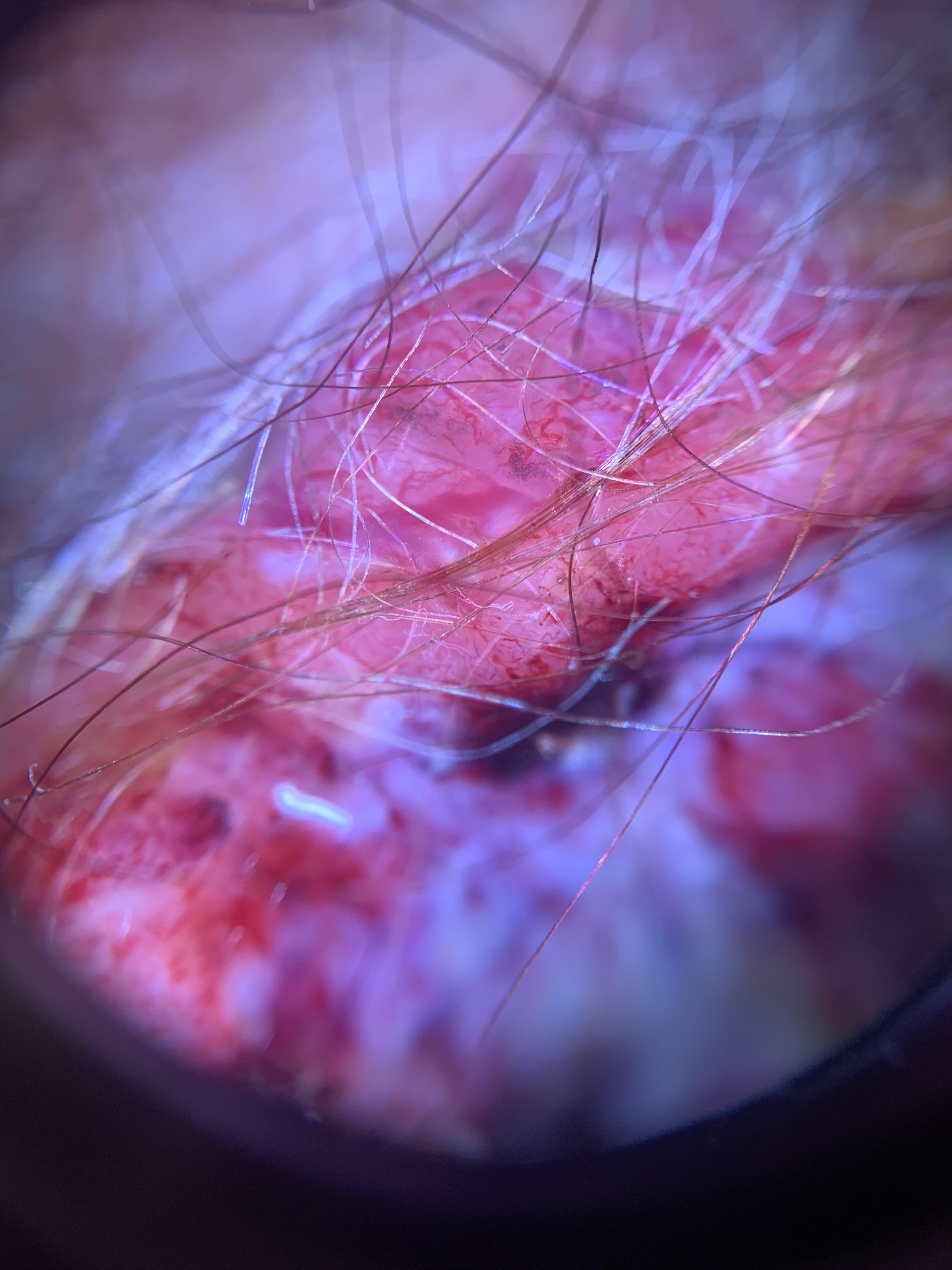| key | value |
|---|---|
| imaging | dermoscopic image |
| subject | female, roughly 85 years of age or older |
| site | the head or neck |
| diagnostic label | Squamous cell carcinoma (biopsy-proven) |